The contributor is a female aged 50–59, this image was taken at a distance — 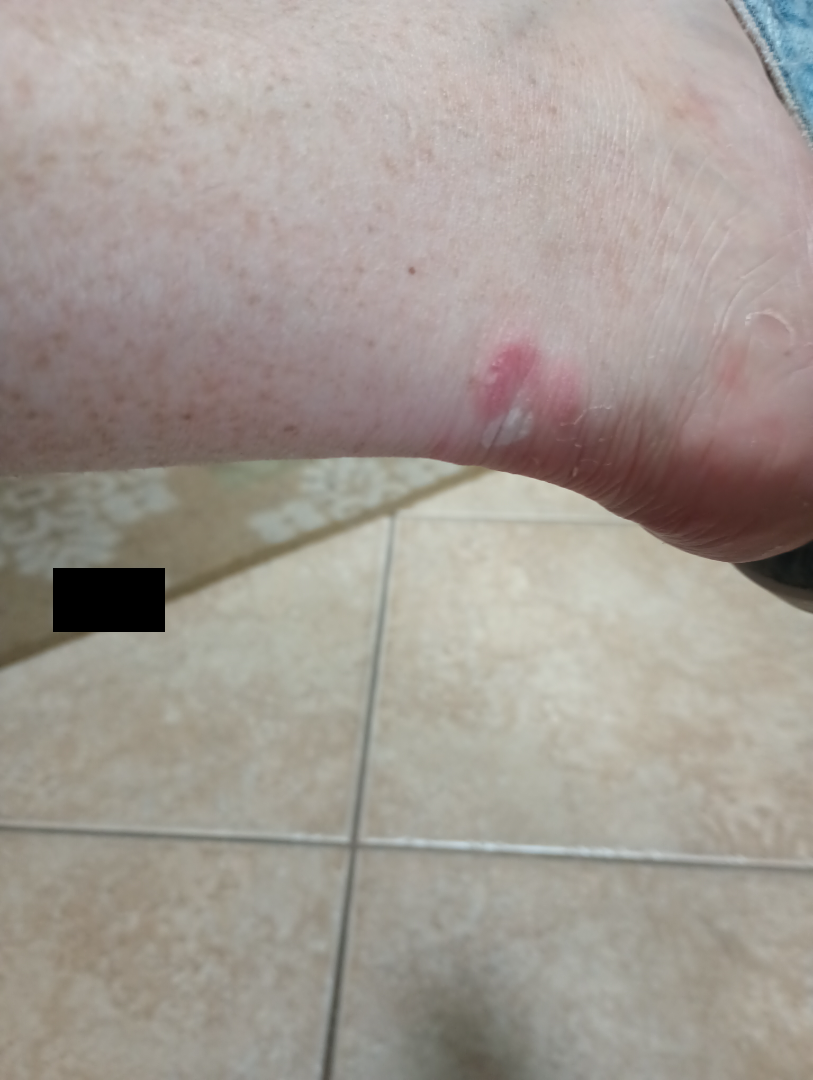Notes:
• assessment: not assessable
• skin tone: FST II; non-clinician graders estimated 2 on the Monk skin tone scale
• patient-reported symptoms: enlargement and darkening
• patient's own categorization: a rash
• history: less than one week
• texture: raised or bumpy